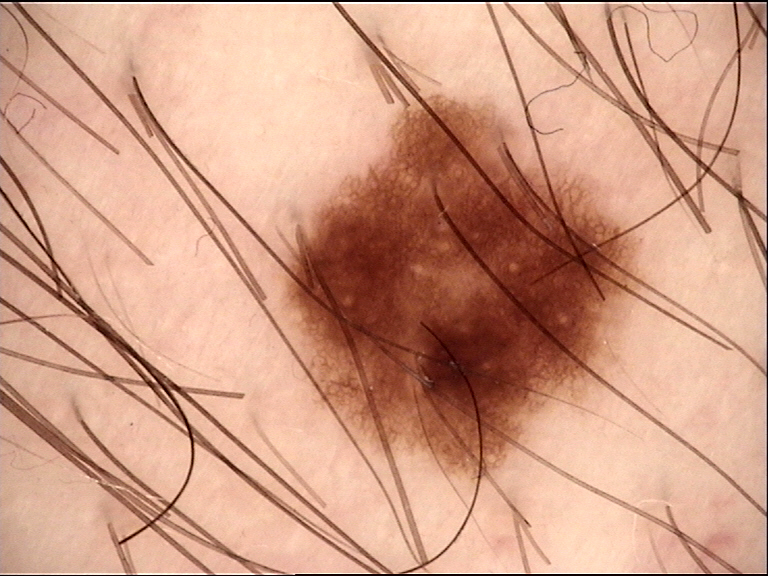assessment=junctional nevus (expert consensus).